A dermoscopy image of a single skin lesion.
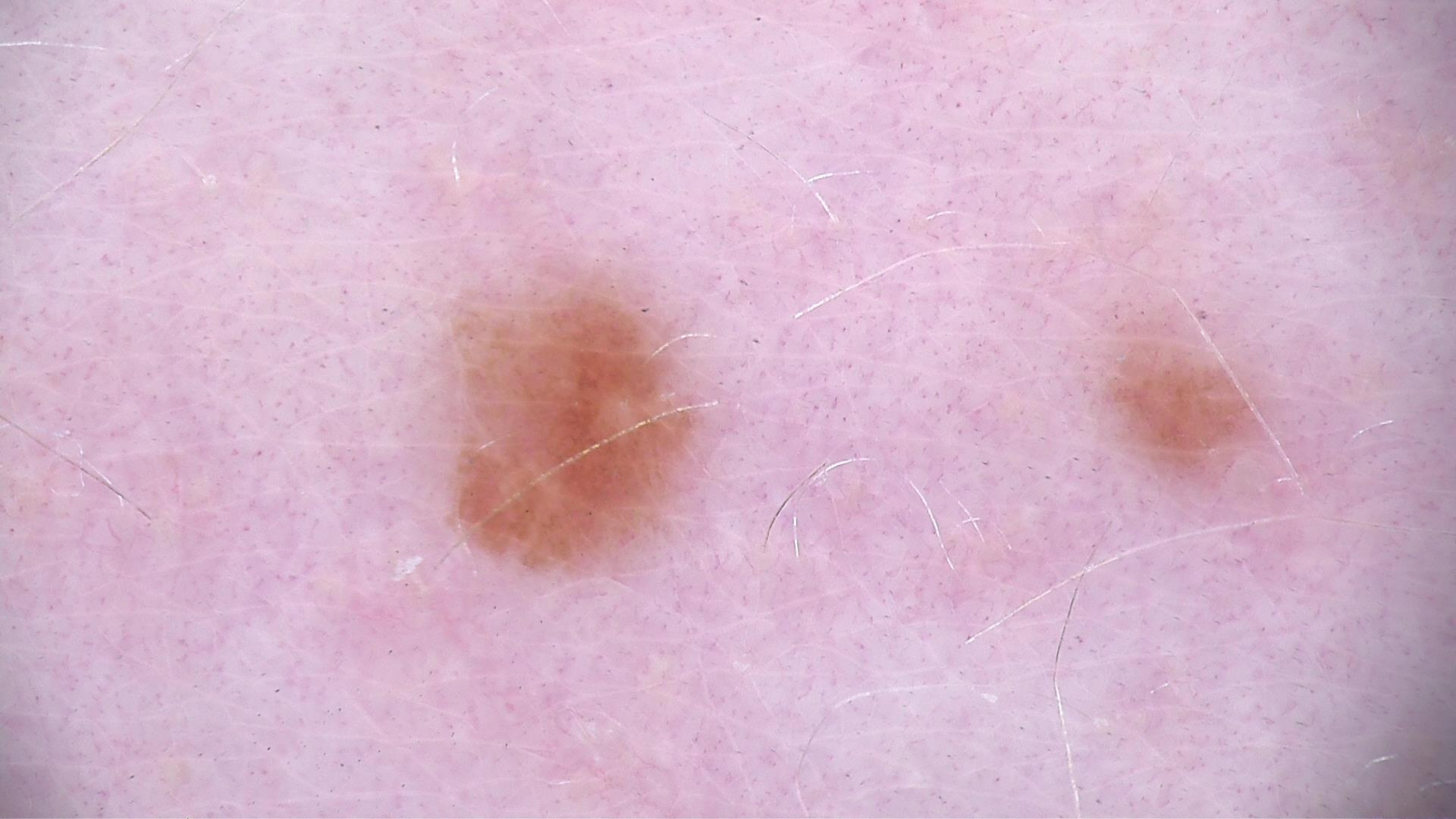Consistent with a dysplastic junctional nevus.